A dermoscopic close-up of a skin lesion: 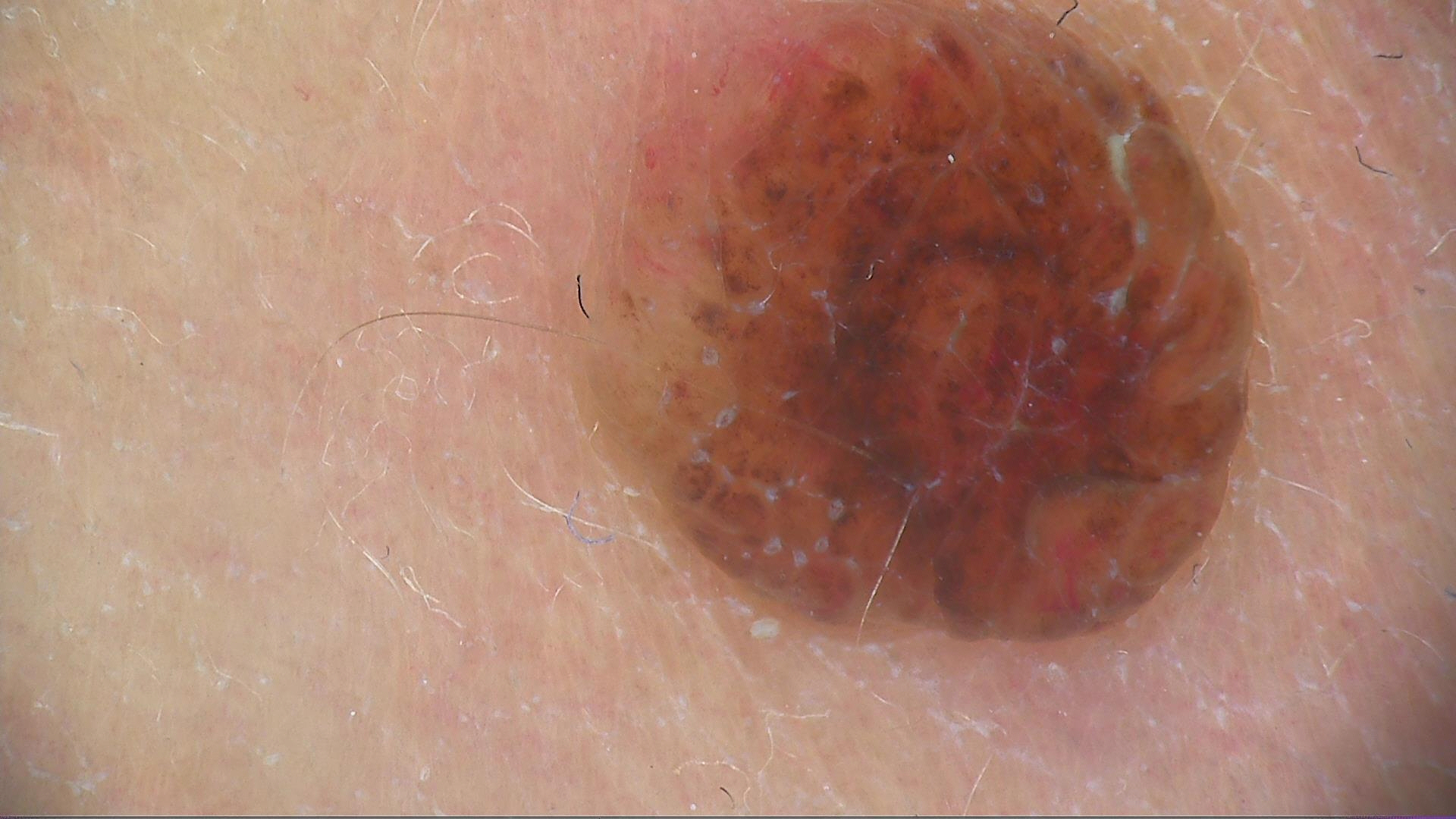Findings:
• label — dermal nevus (expert consensus)